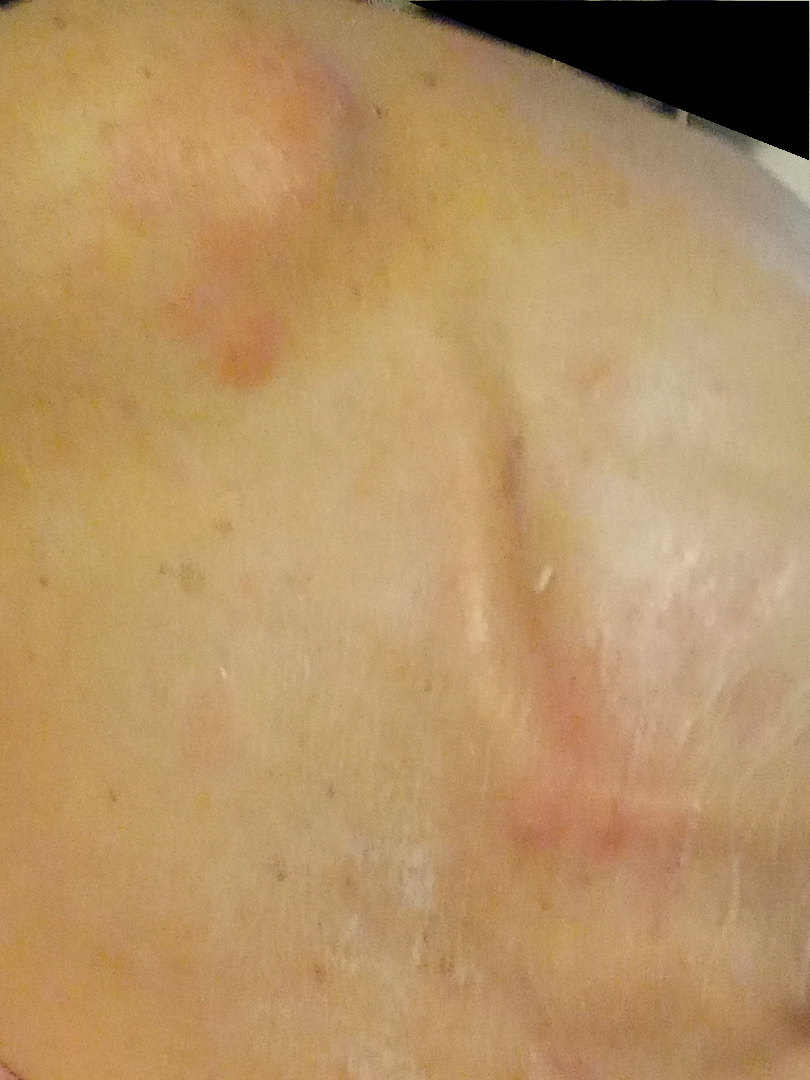Review:
The reviewing dermatologist was unable to assign a differential diagnosis from the image.